A smartphone photograph of a skin lesion; a male patient 71 years of age — 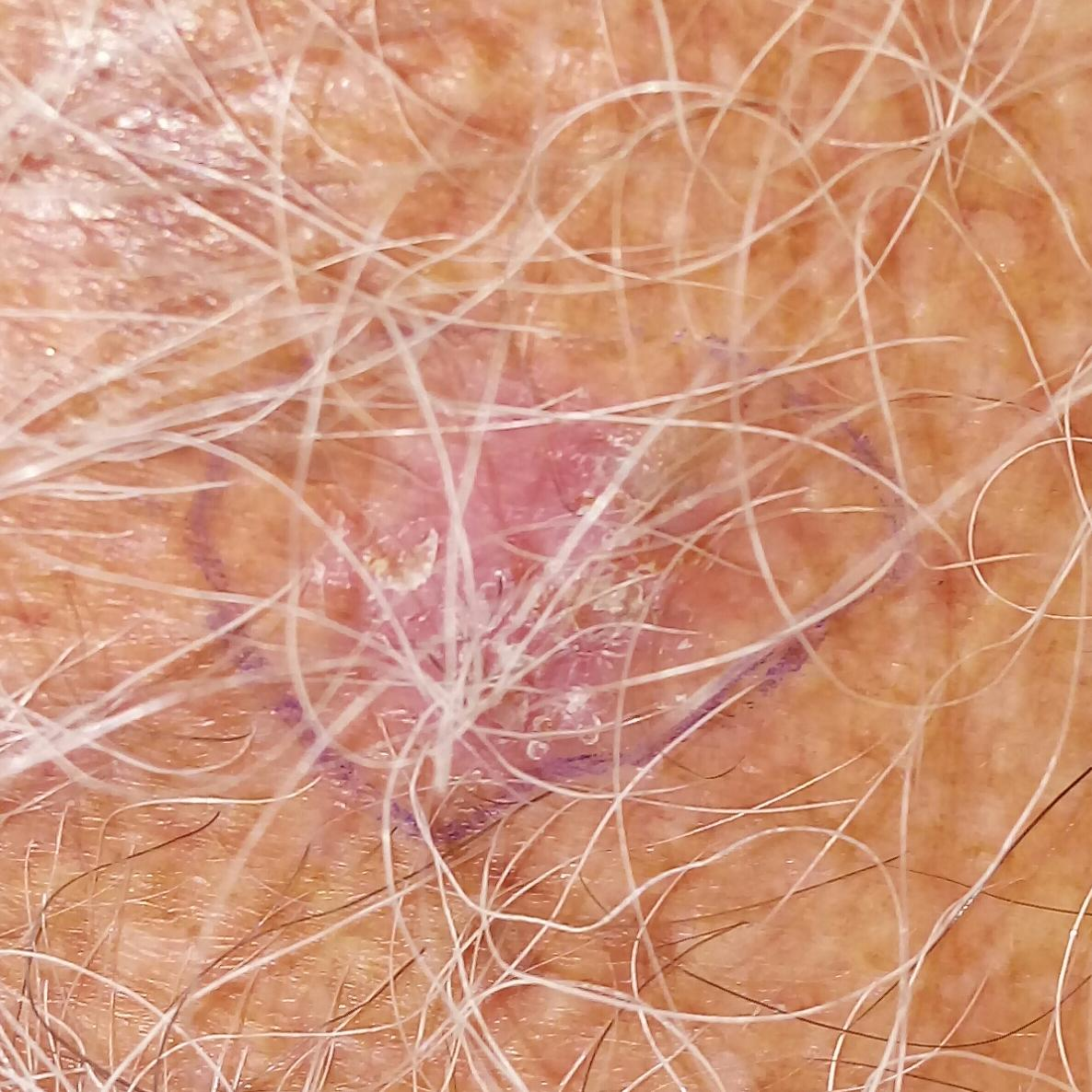The lesion was found on the chest. By the patient's account, the lesion is elevated, itches, and hurts. Histopathological examination showed a basal cell carcinoma.